A dermoscopic close-up of a skin lesion · a male subject, aged approximately 80: 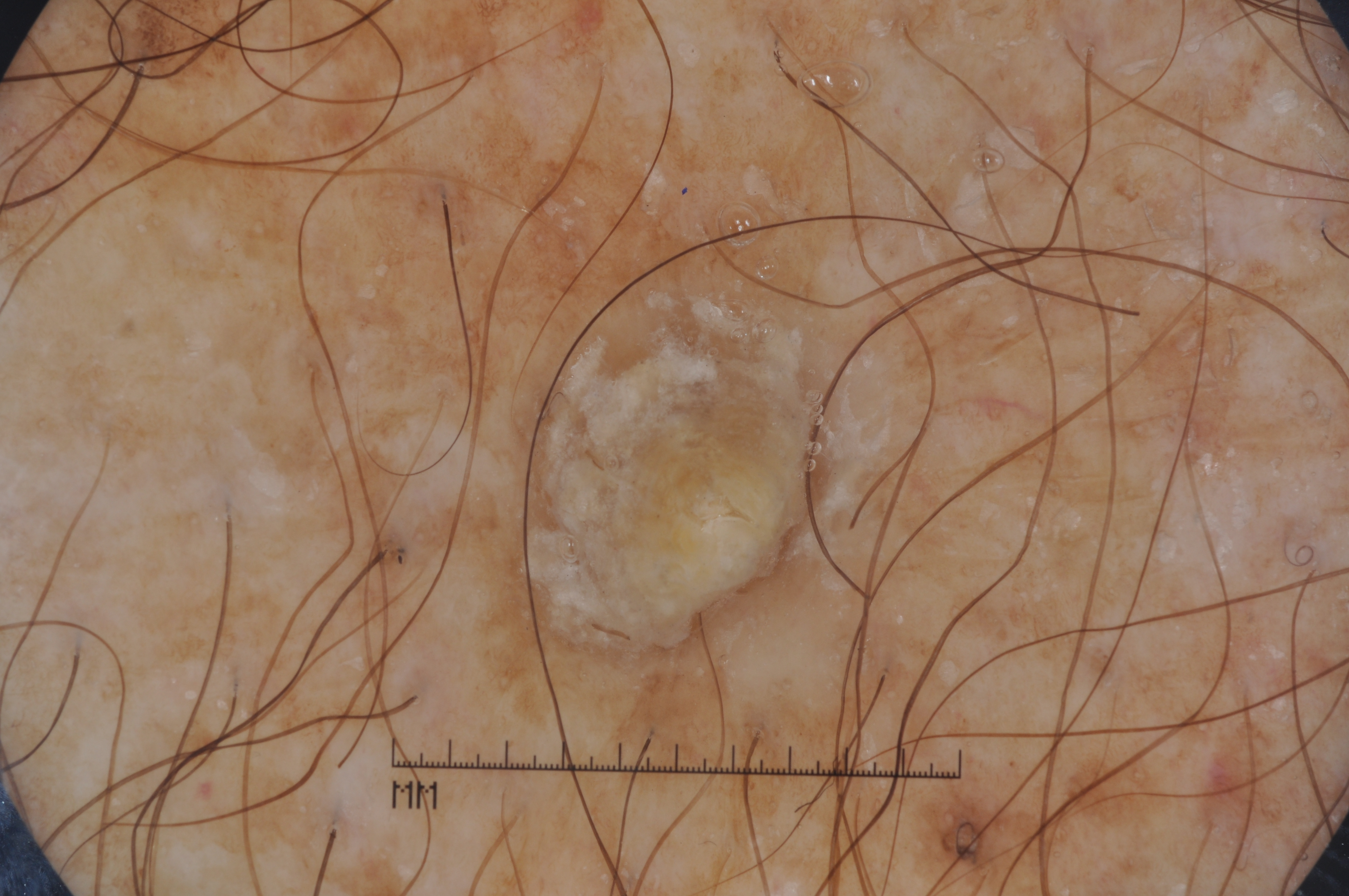Case summary: The lesion is bounded by x1=442, y1=249, x2=877, y2=691. Dermoscopic examination shows no pigment network, milia-like cysts, negative network, or streaks. Impression: The diagnostic assessment was a melanocytic nevus.